Close-up view · the patient is a female aged 50–59 · the affected area is the front of the torso.
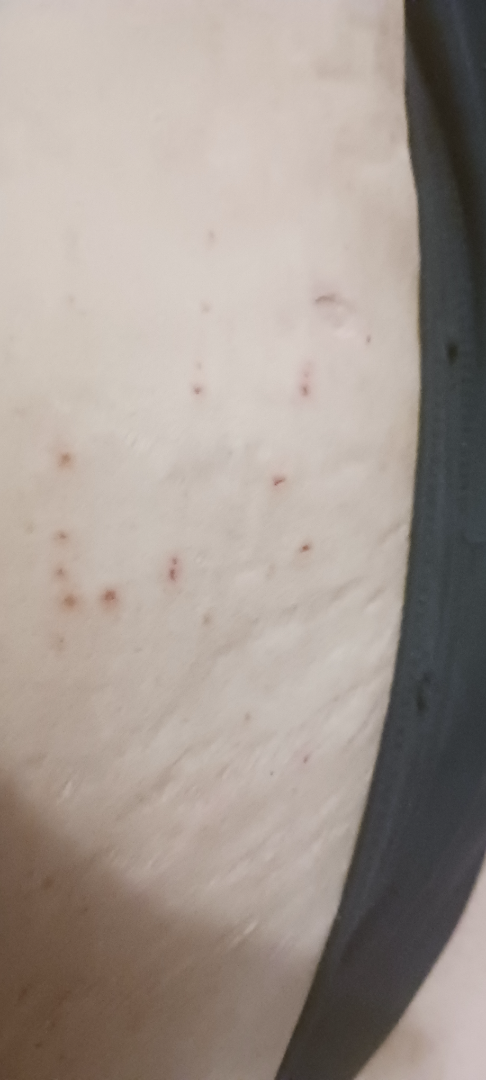Assessment:
The case was difficult to assess from the available photograph.
Clinical context:
The patient considered this a rash. The contributor notes the lesion is raised or bumpy. Reported duration is less than one week.